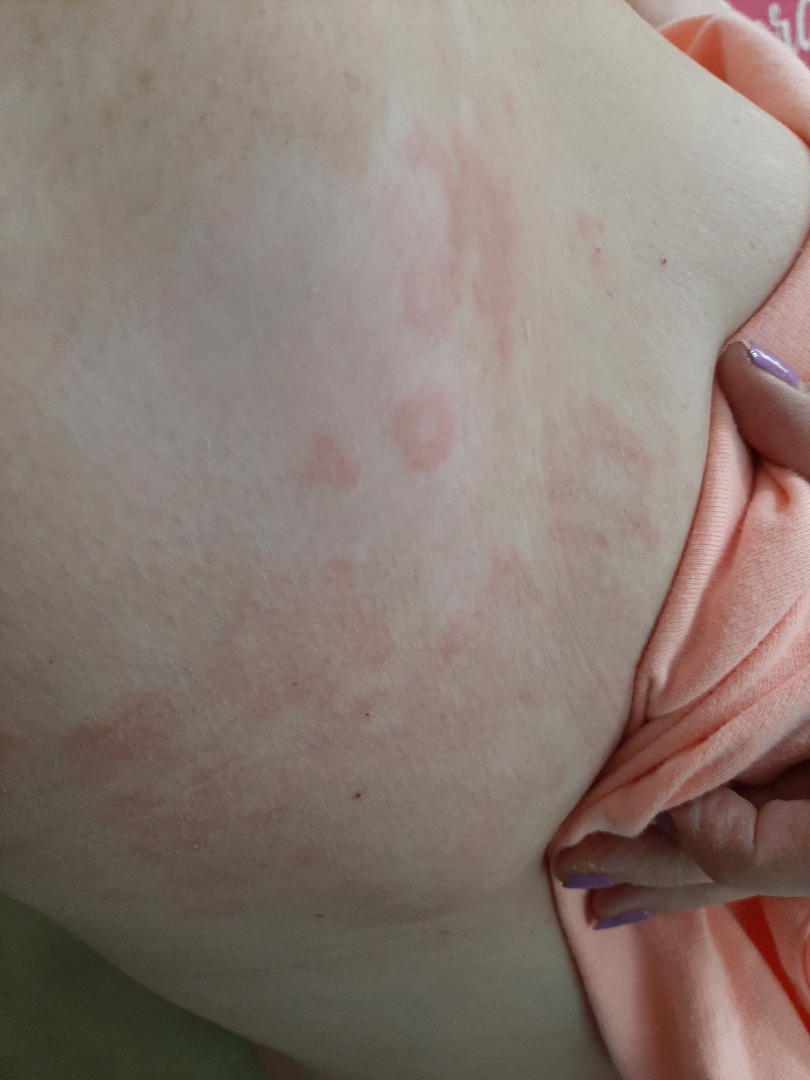assessment = not assessable; skin tone = lay reviewers estimated 2 on the MST; photo taken = close-up.